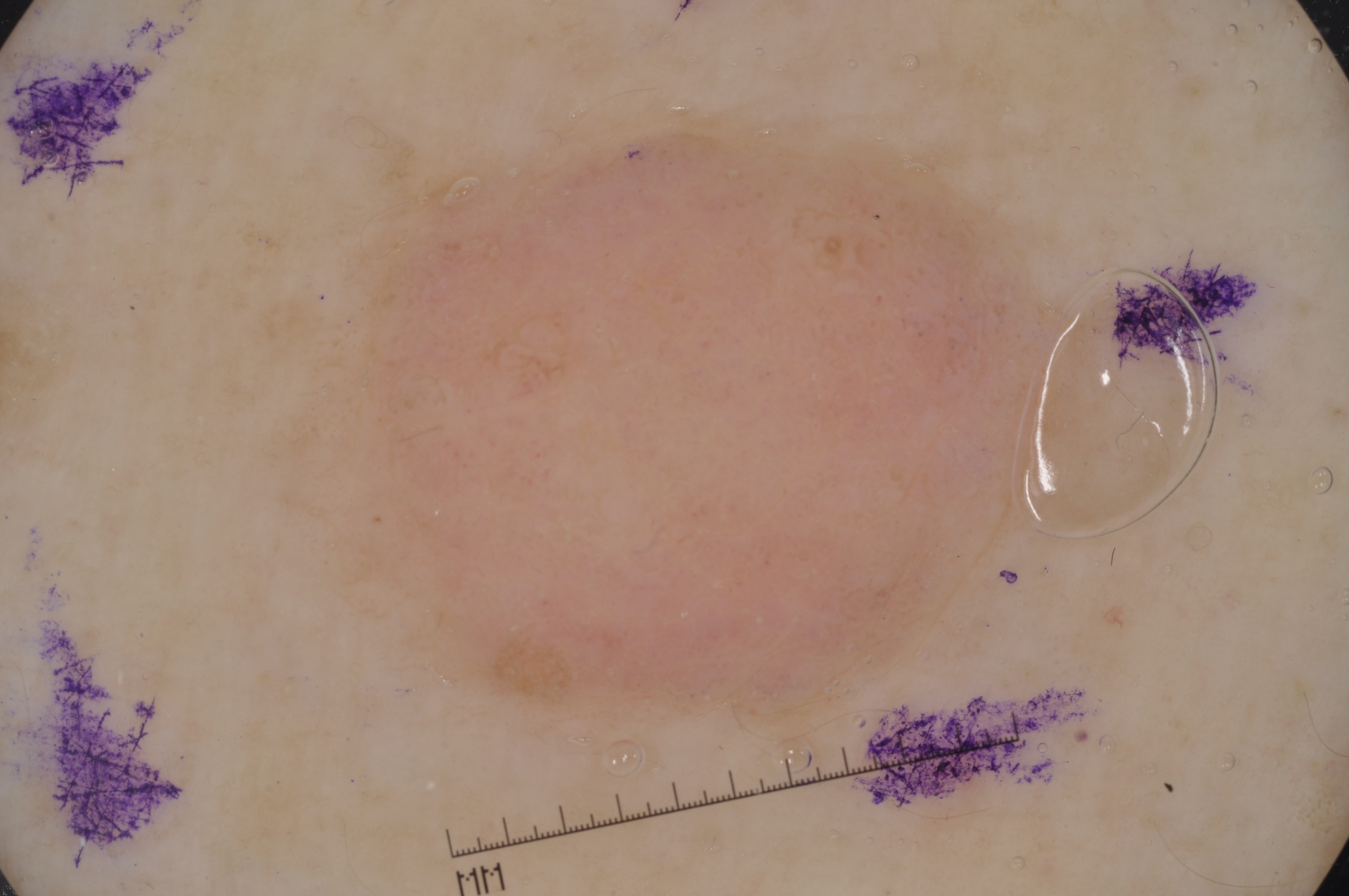Q: Who is the patient?
A: male, aged 68 to 72
Q: What kind of image is this?
A: dermoscopy of a skin lesion
Q: What is the lesion's bounding box?
A: [282,114,1086,746]
Q: Which assessed dermoscopic features were absent?
A: streaks, milia-like cysts, pigment network, and negative network
Q: How much of the field does the lesion occupy?
A: large
Q: What is this lesion?
A: a melanocytic nevus